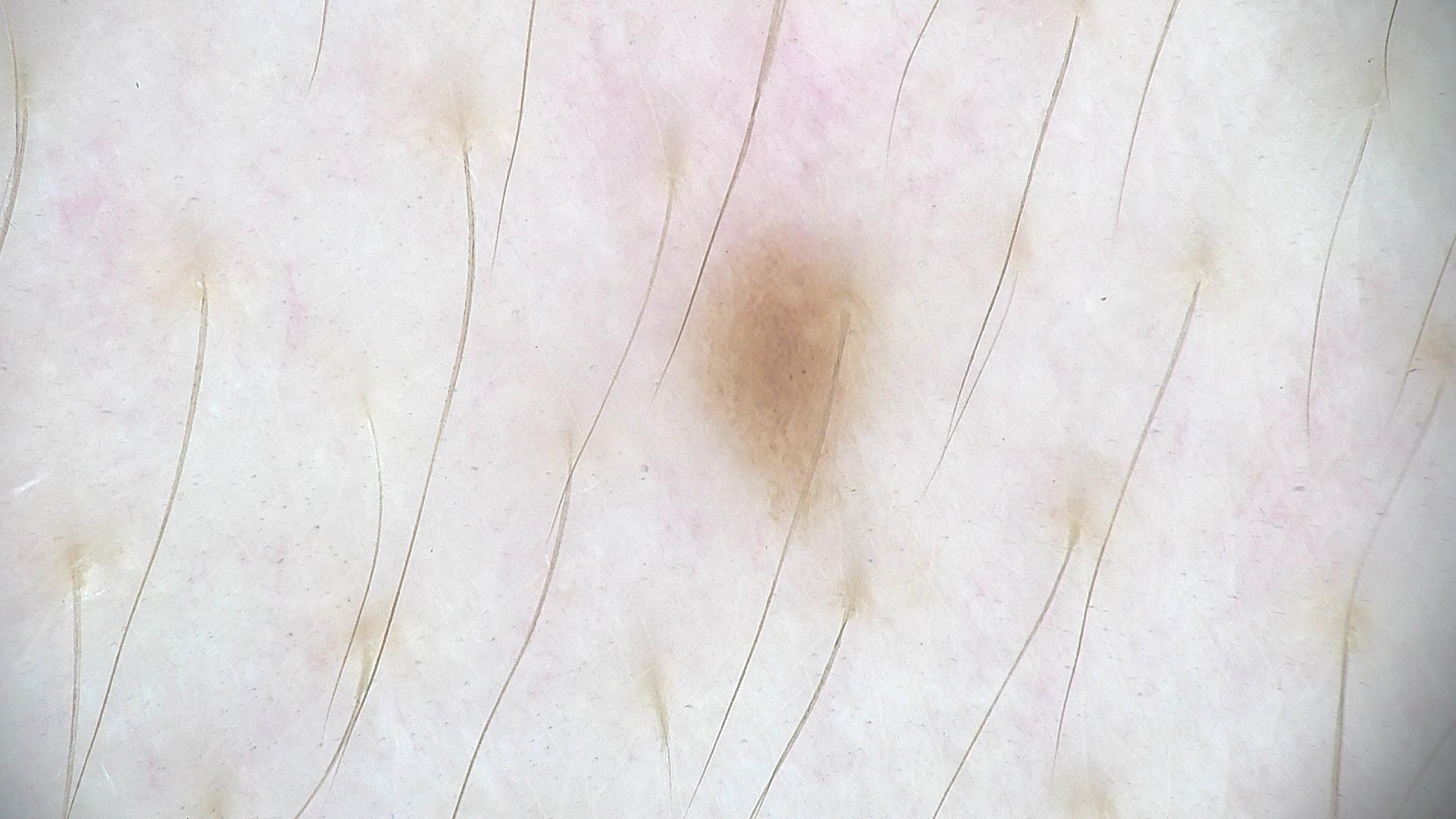A dermoscopic photograph of a skin lesion. The diagnosis was a dysplastic junctional nevus.